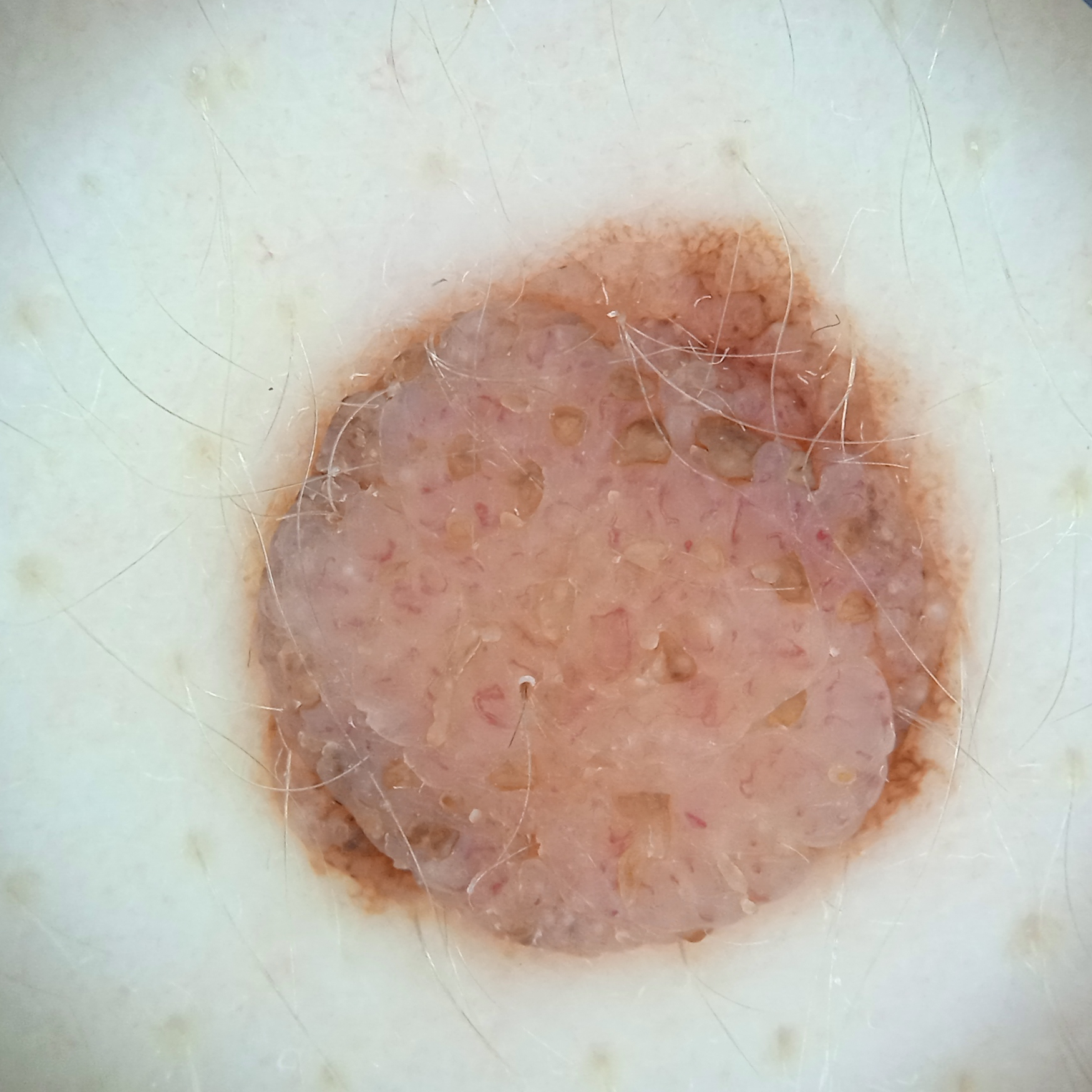Q: What is the imaging modality?
A: dermoscopy
Q: Tell me about the patient.
A: female, age 26
Q: What is the patient's nevus burden?
A: numerous melanocytic nevi
Q: What are the relevant risk factors?
A: a history of sunbed use
Q: What is the anatomic site?
A: the back
Q: Lesion size?
A: 8.9 mm
Q: What was the diagnosis?
A: melanocytic nevus (dermatologist consensus)